Collected as part of a research study, without a referral diagnosis · dermoscopy of a skin lesion · a female subject age 26 — 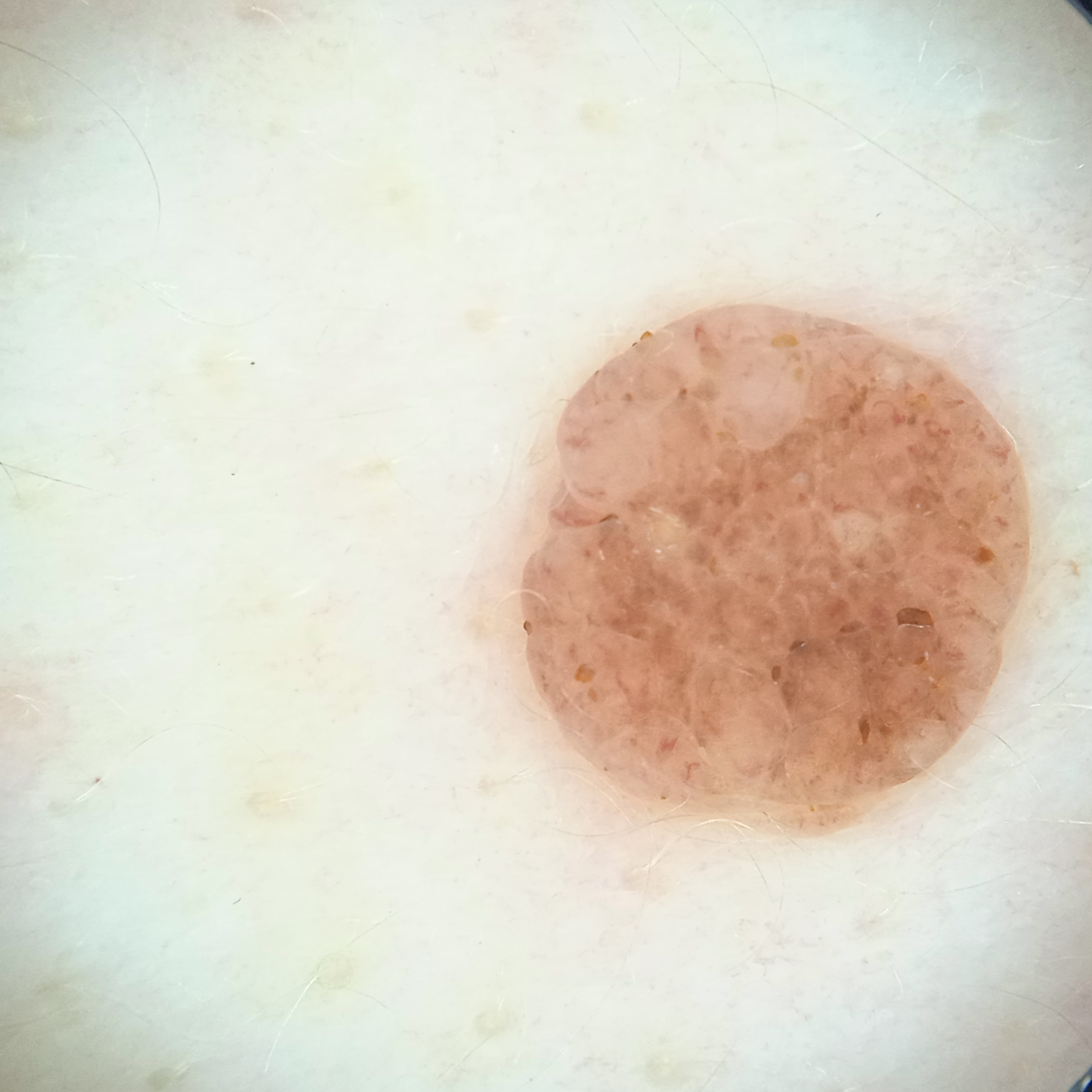The lesion is on the back. Measuring roughly 5.6 mm. Dermatologist review favored a melanocytic nevus.